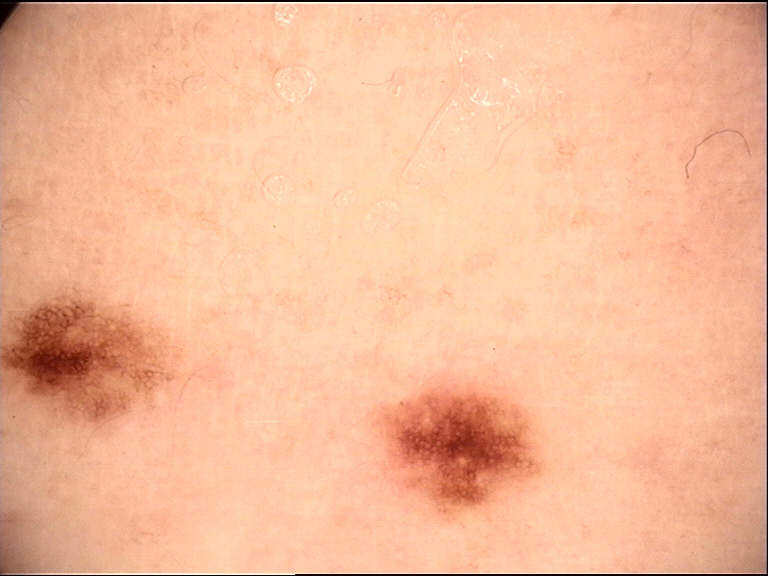diagnosis=dysplastic junctional nevus (expert consensus).